Female subject, age 18–29. This is a close-up image.
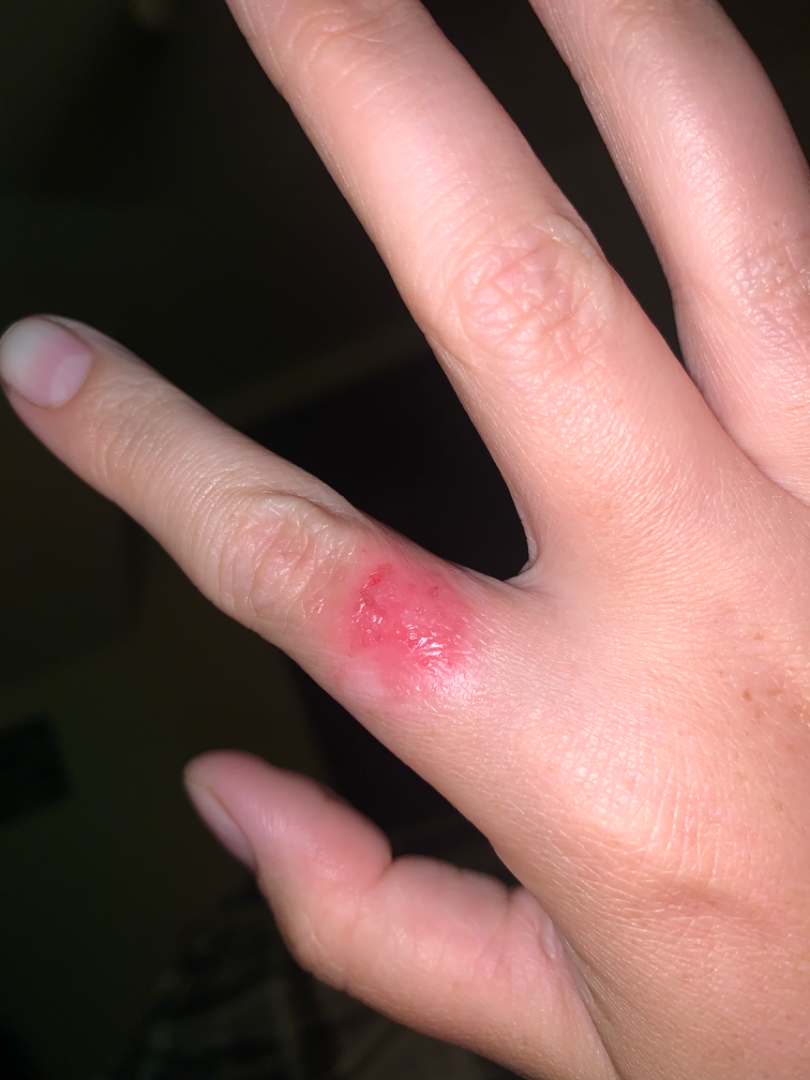Findings:
– skin tone · Fitzpatrick phototype I; lay graders estimated 2 on the MST
– duration · one to three months
– patient's own categorization · a rash
– reported symptoms · bothersome appearance, burning, bleeding, enlargement and pain
– differential · Impetigo and Skin and soft tissue atypical mycobacterial infection were each considered, in no particular order; less likely is Deep fungal infection